The patient described the issue as a rash. The lesion involves the leg. The lesion is described as flat, rough or flaky and raised or bumpy. Symptoms reported: itching. Close-up view.
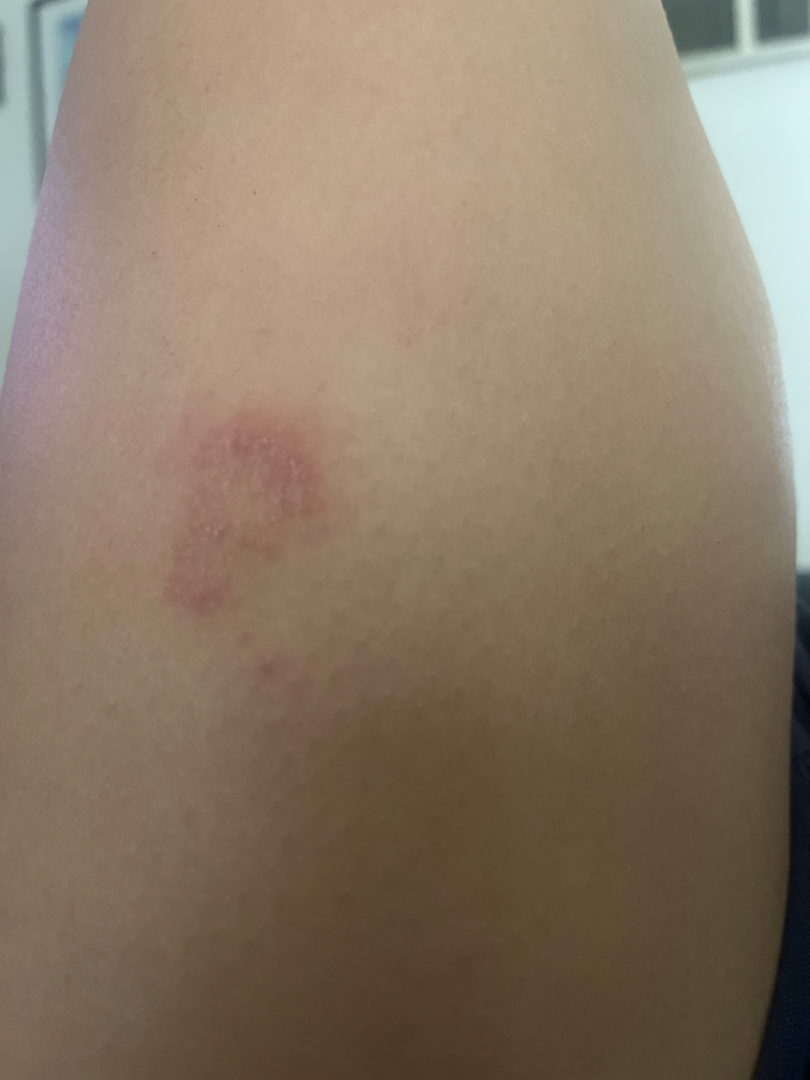The image was not sufficient for the reviewer to characterize the skin condition.